A dermoscopic image of a skin lesion:
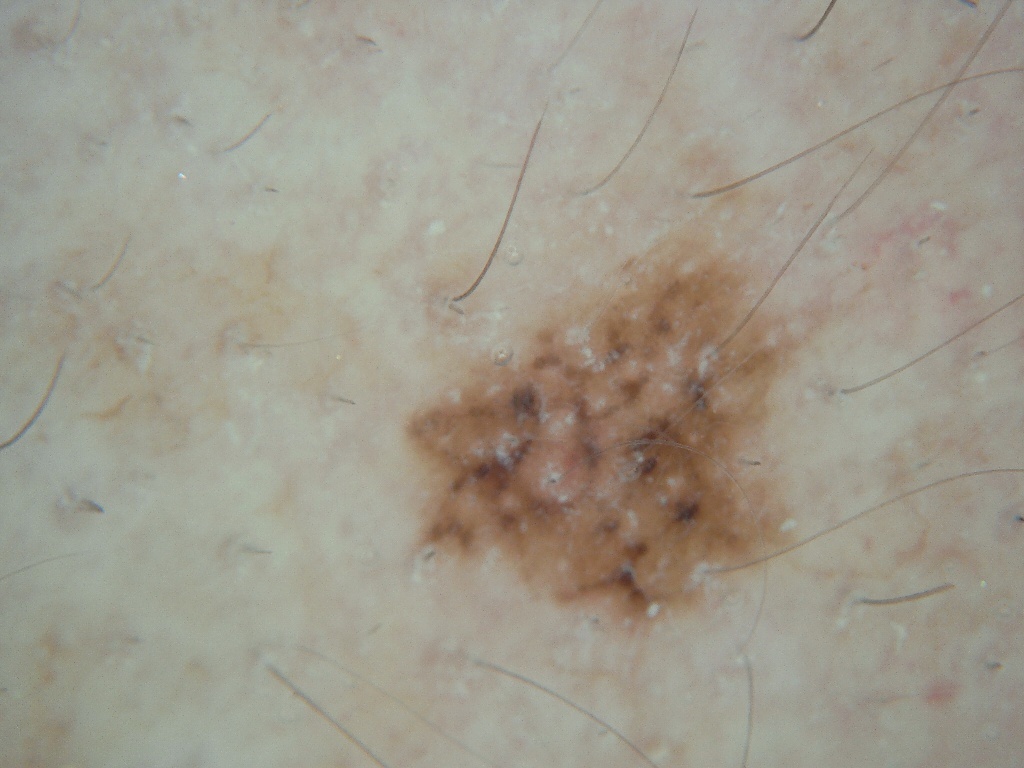Findings:
On dermoscopy, the lesion shows neither streaks nor globules. The lesion takes up a moderate portion of the field. The lesion is bounded by 406 242 797 637.
Pathology:
On biopsy, the diagnosis was a malignant skin lesion.